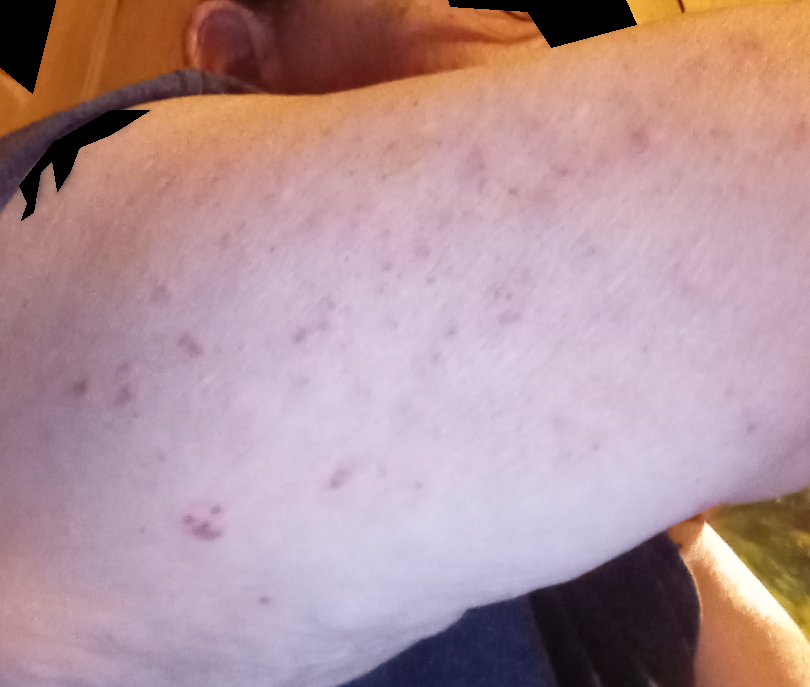assessment: ungradable on photographic review
contributor: female, age 60–69
photo taken: at a distance
other reported symptoms: none reported
affected area: head or neck and arm
surface texture: raised or bumpy